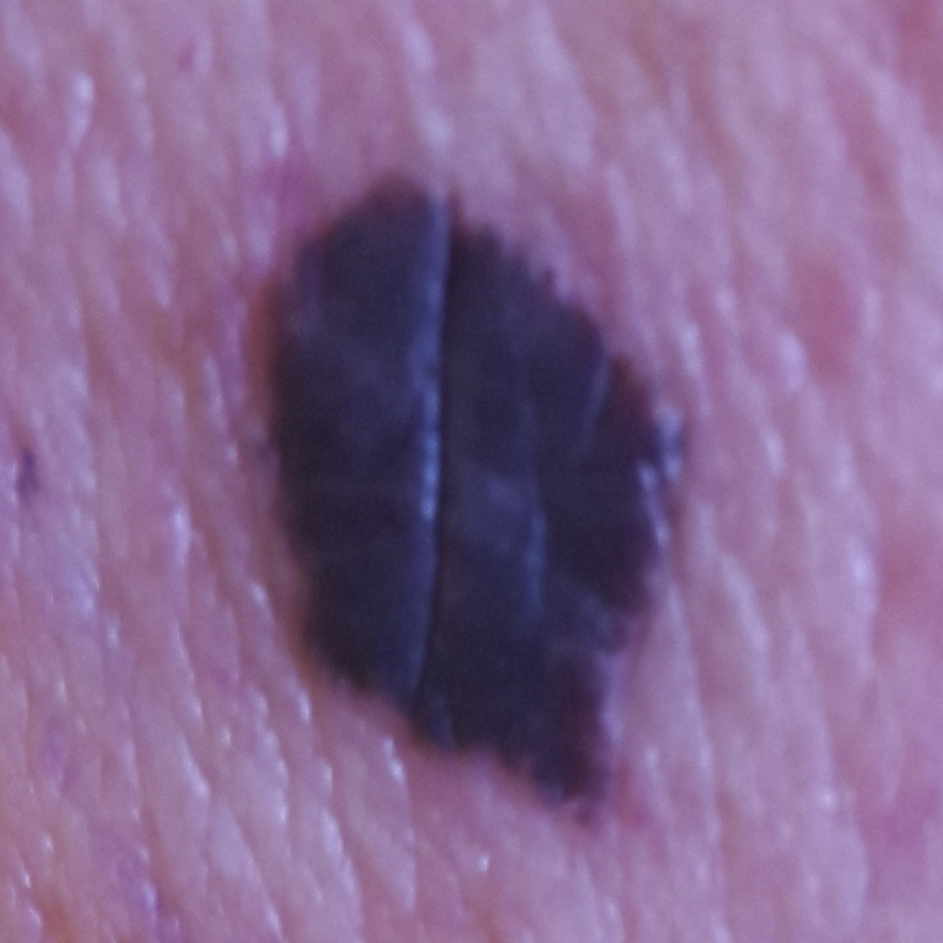Case:
– subject — female, 55 years old
– imaging — smartphone clinical photo
– anatomic site — the chest
– symptoms — no growth
– diagnostic label — melanoma (biopsy-proven)